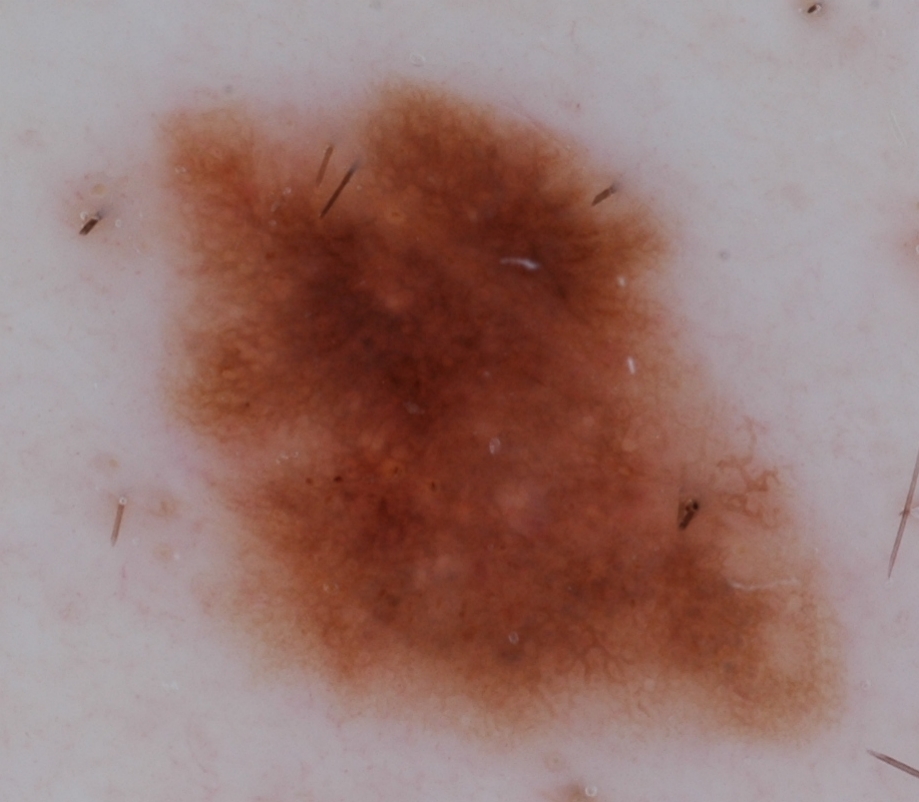A skin lesion imaged with a dermatoscope. Lesion location: 146, 77, 840, 743. The lesion covers approximately 45% of the dermoscopic field. Dermoscopic assessment notes pigment network and globules, with no negative network, streaks, or milia-like cysts. The diagnostic assessment was a melanocytic nevus.